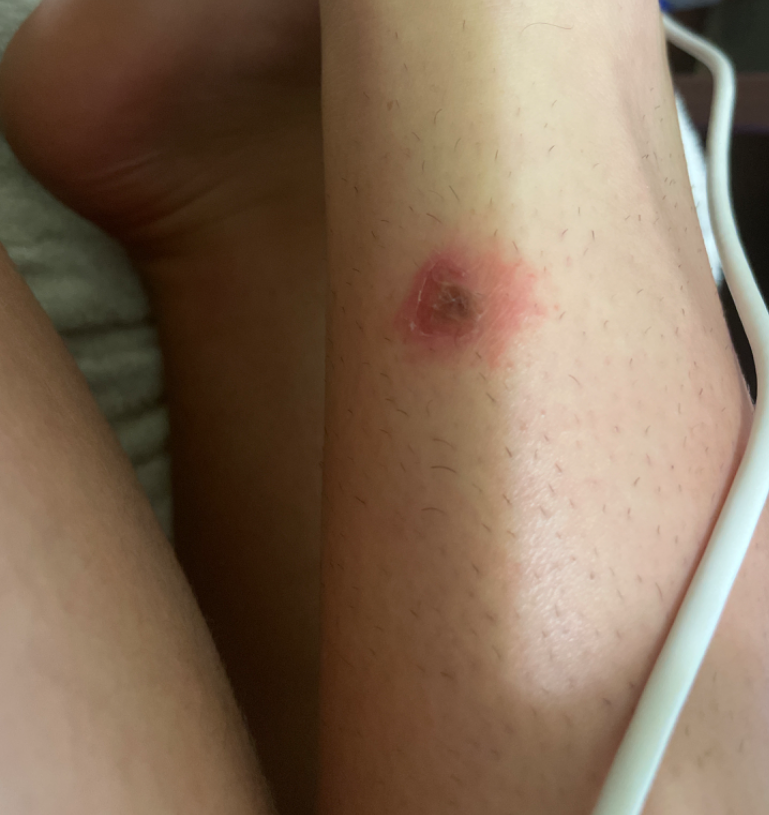Impression:
The case was difficult to assess from the available photograph.
History:
Human graders estimated Monk Skin Tone 3. The photograph is a close-up of the affected area.